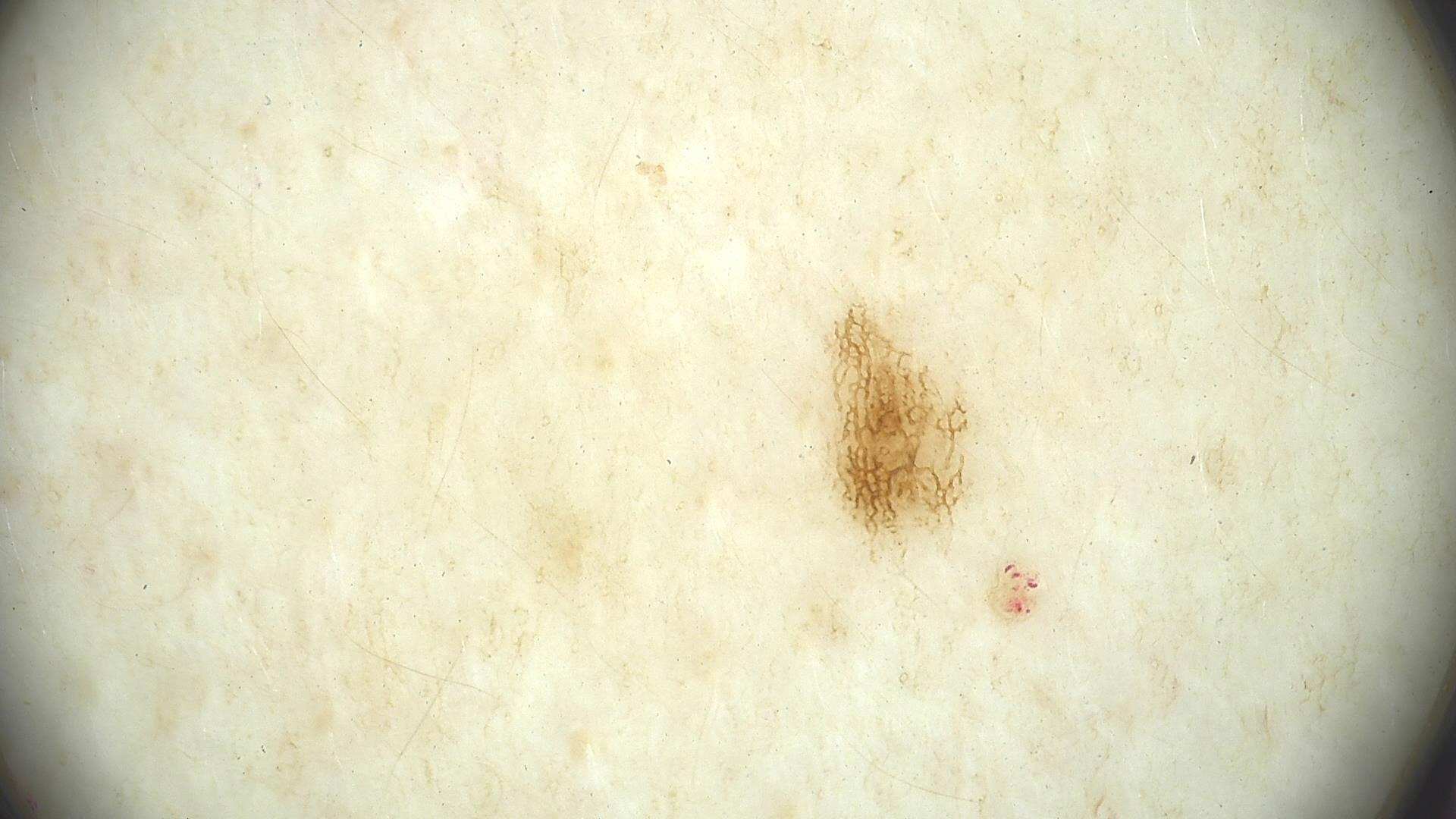A dermoscopic close-up of a skin lesion. Consistent with a benign lesion — a dysplastic junctional nevus.